A dermoscopy image of a single skin lesion: 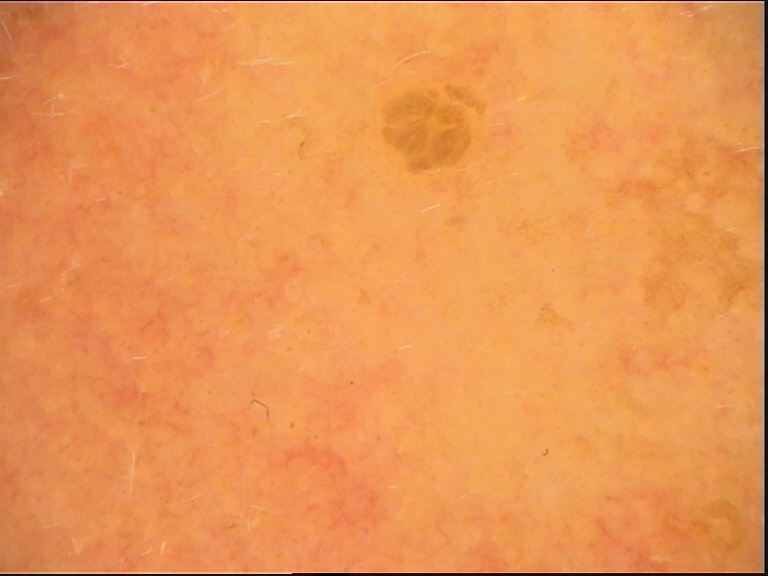Conclusion: Diagnosed as a keratinocytic lesion — a seborrheic keratosis.